A patient aged 39. A clinical close-up photograph of a skin lesion.
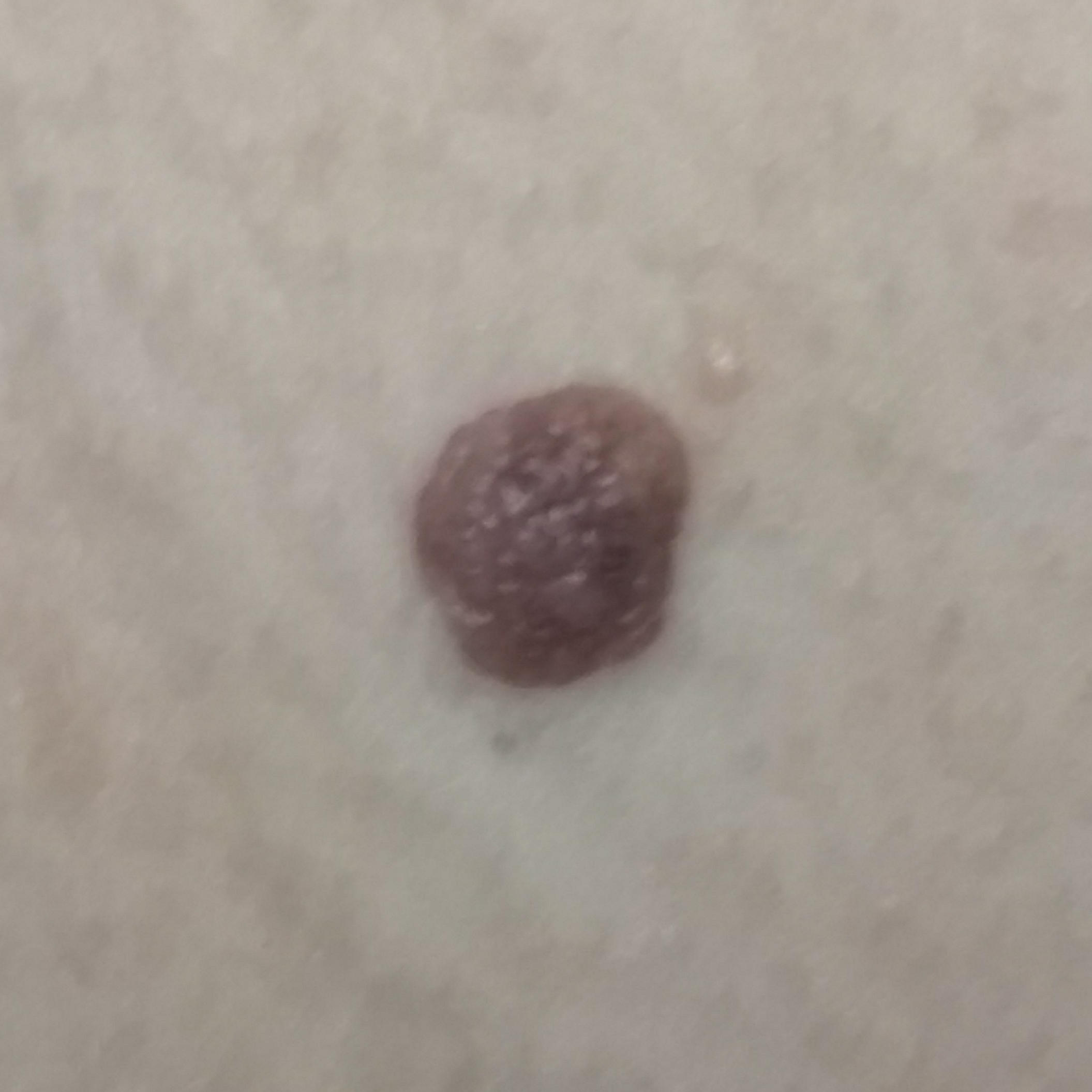  lesion_location: the neck
  diagnosis:
    name: nevus
    code: NEV
    malignancy: benign
    confirmation: clinical consensus